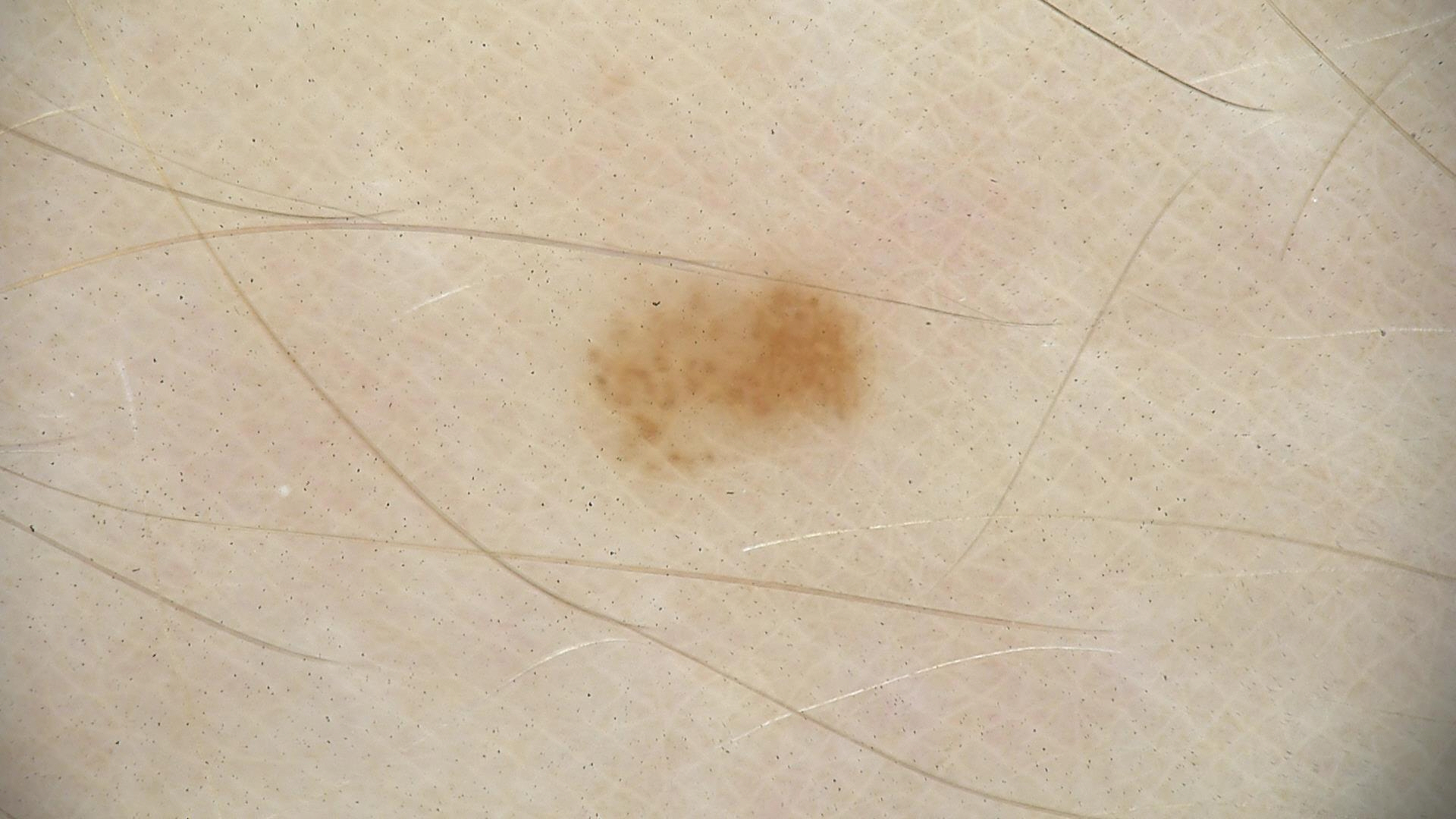Summary:
A dermoscopic close-up of a skin lesion.
Impression:
Diagnosed as a benign lesion — a dysplastic junctional nevus.